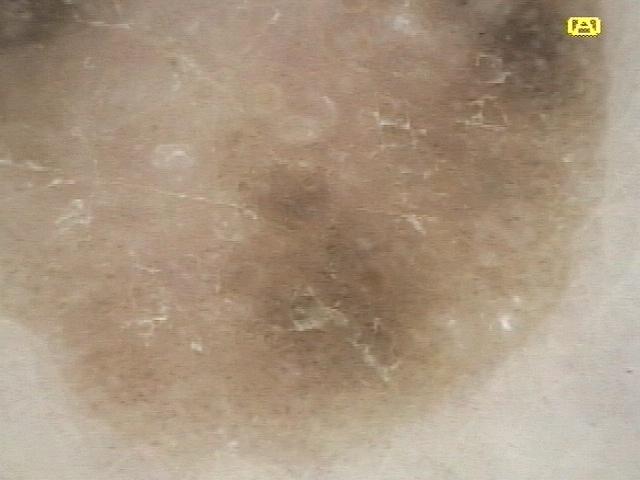image type=dermatoscopic image; location=the trunk (the posterior trunk); assessment=Seborrheic keratosis.